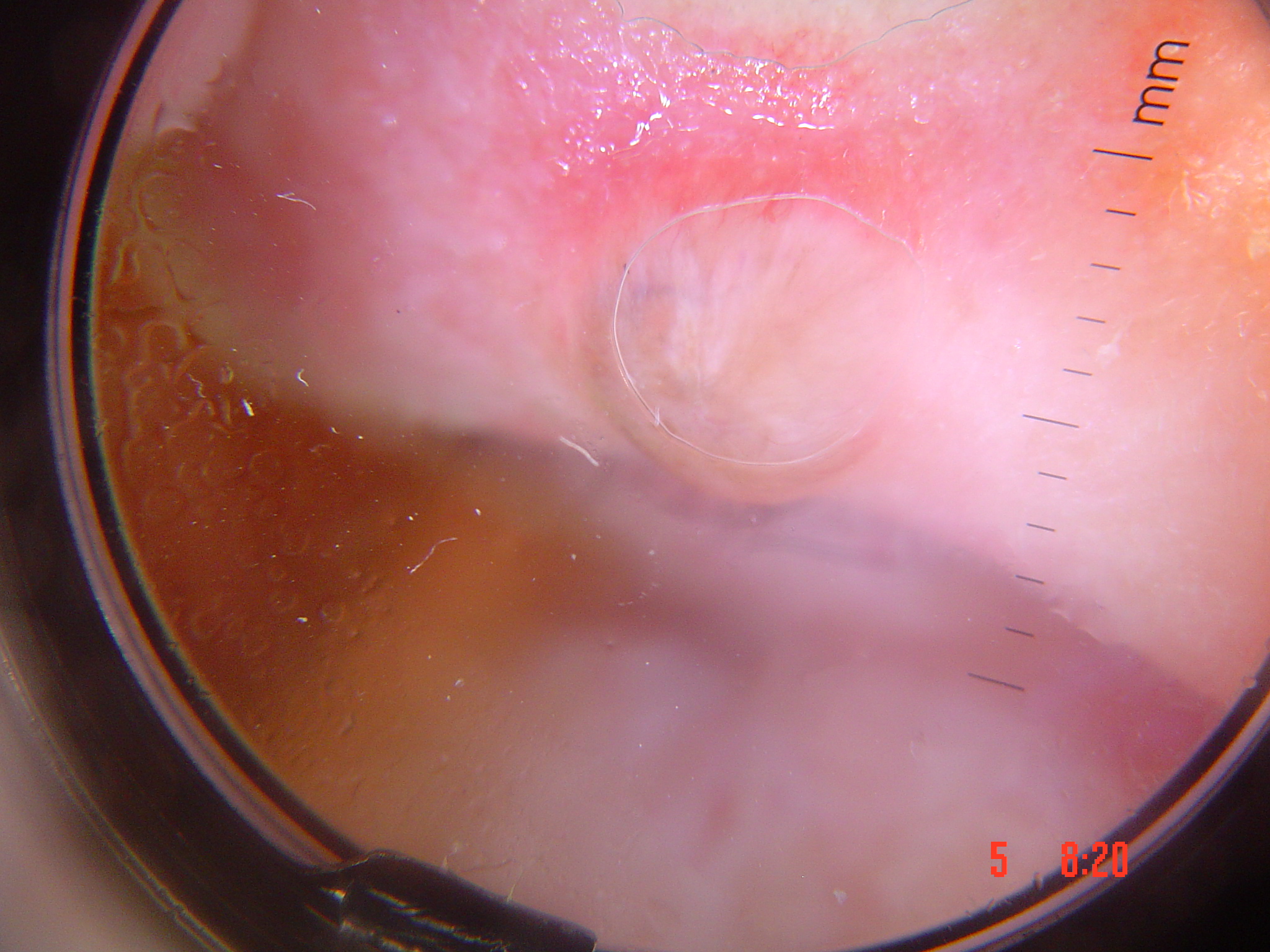Confirmed on histopathology as a basal cell carcinoma.